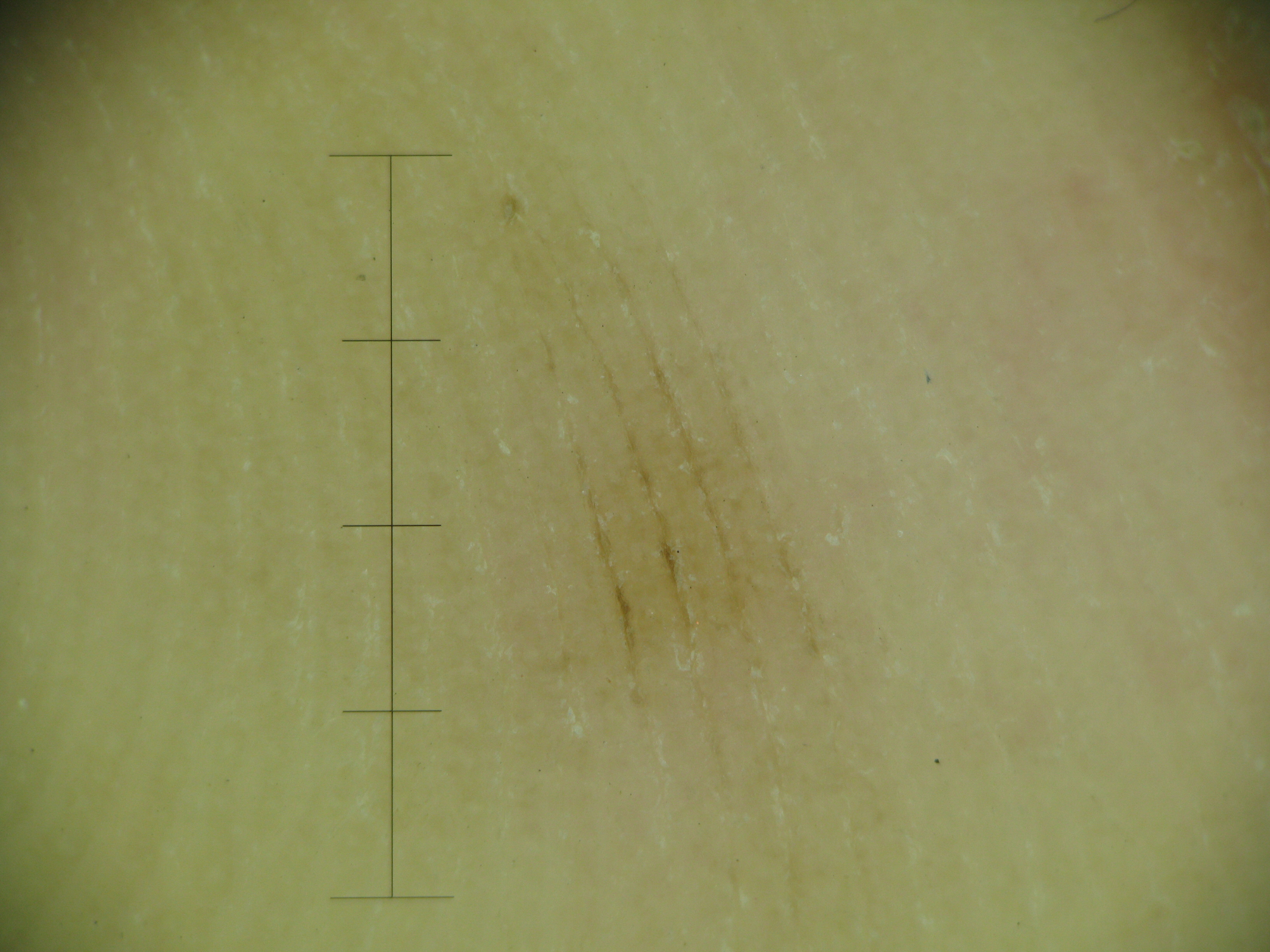Case: A dermoscopic image of a skin lesion. Conclusion: Labeled as a banal lesion — an acral junctional nevus.